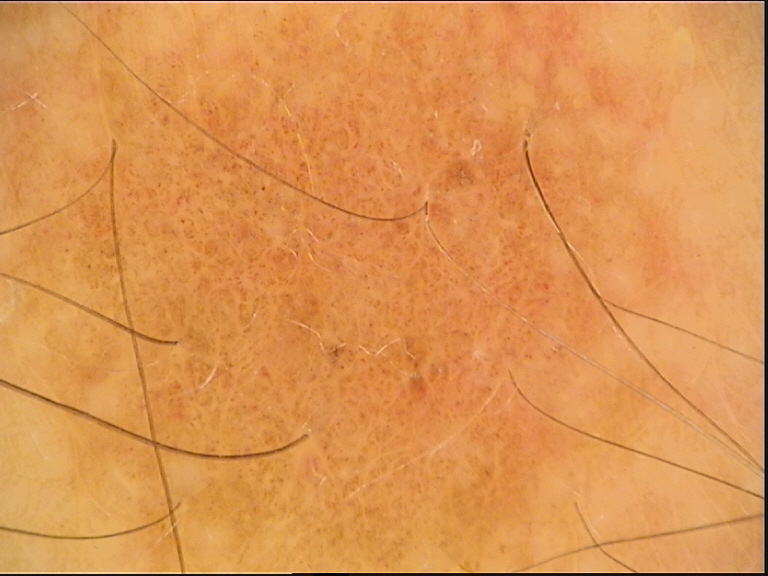A dermoscopic photograph of a skin lesion.
Diagnosed as a dysplastic junctional nevus.